The photo was captured at an angle · male subject, age 70–79 · the lesion involves the arm and front of the torso:
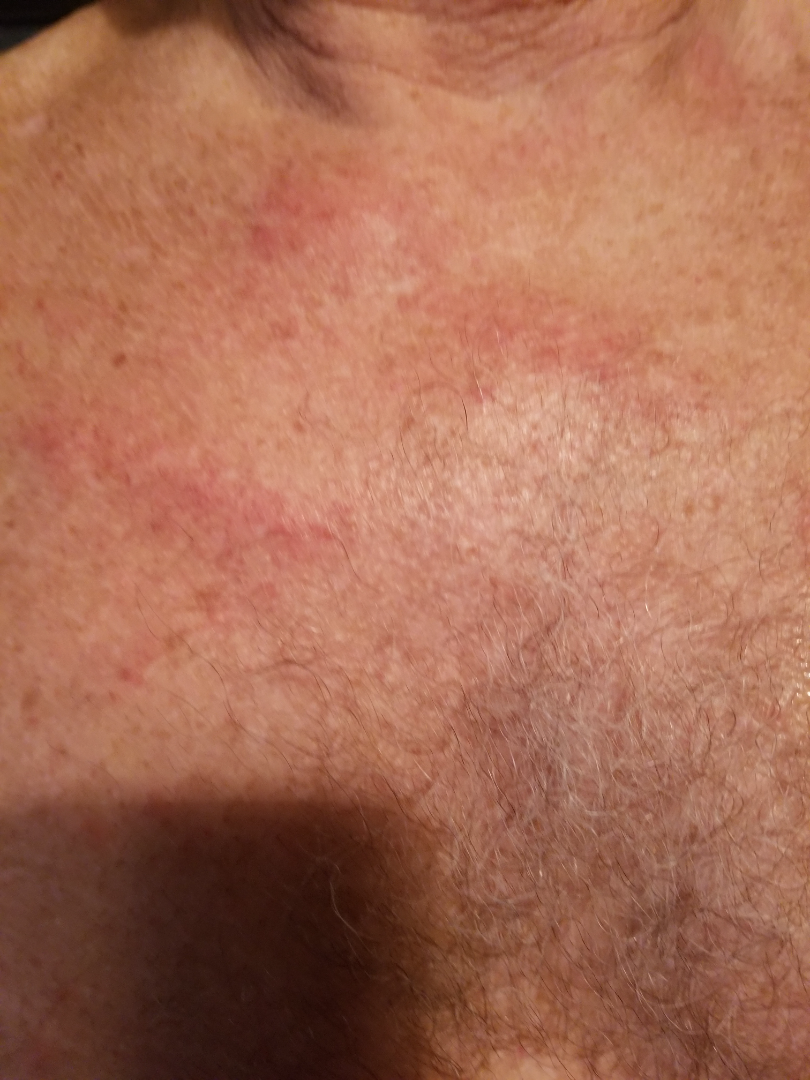<case>
<duration>less than one week</duration>
<symptoms>itching, bothersome appearance</symptoms>
<texture>raised or bumpy, rough or flaky</texture>
<patient_category>a rash</patient_category>
<systemic_symptoms>none reported</systemic_symptoms>
<differential>
  <tied_lead>Eczema, Allergic Contact Dermatitis</tied_lead>
</differential>
</case>